A dermoscopic image of a skin lesion: 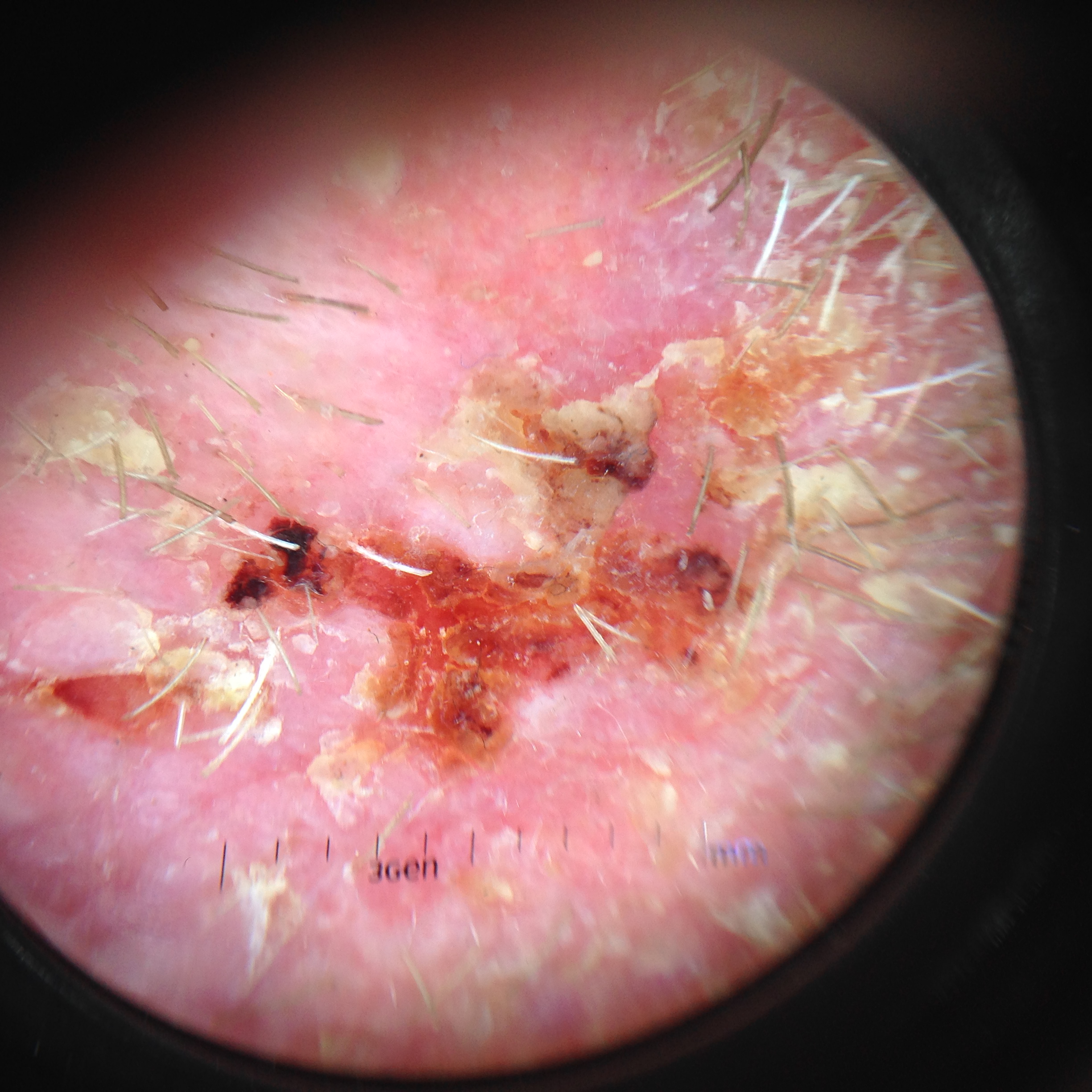diagnostic label = squamous cell carcinoma (biopsy-proven).